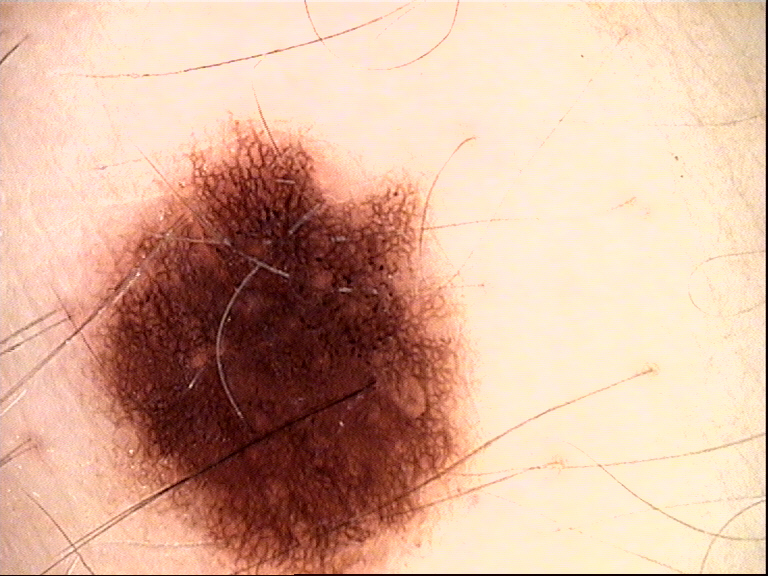Consistent with a benign lesion — a dysplastic junctional nevus.